A female subject, in their mid- to late 60s · a dermoscopy image of a single skin lesion: 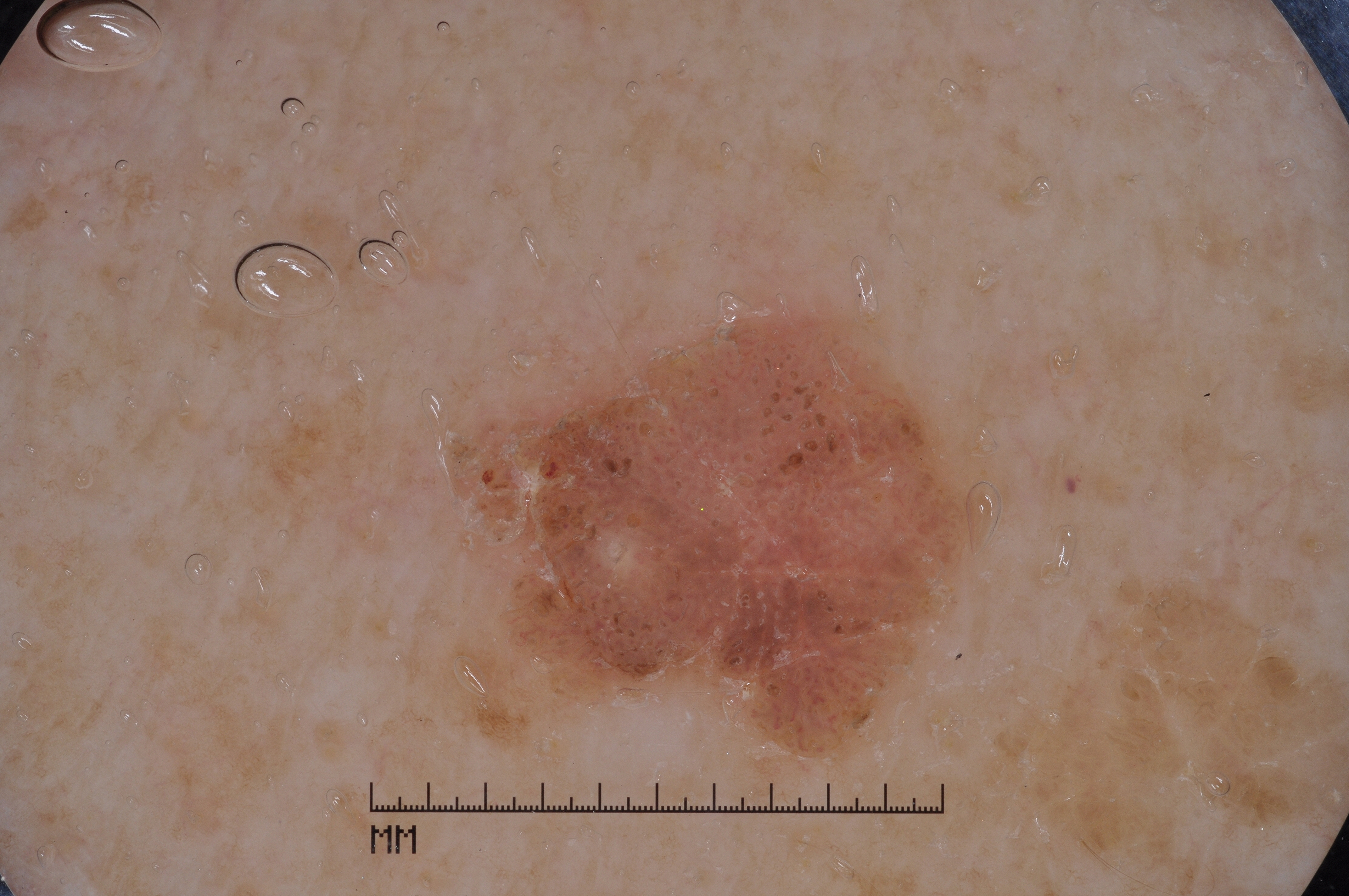Q: What dermoscopic features are present?
A: milia-like cysts; absent: negative network, streaks, and pigment network
Q: How large is the lesion within the image?
A: moderate
Q: Where is the lesion in the image?
A: <box>464, 309, 980, 749</box>
Q: What is the diagnosis?
A: a seborrheic keratosis, a benign lesion